Female patient, age 40–49 · the arm is involved · the photograph was taken at an angle: 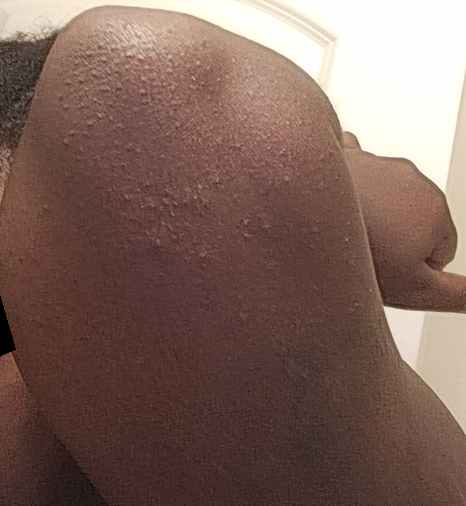Most consistent with Keratosis pilaris.